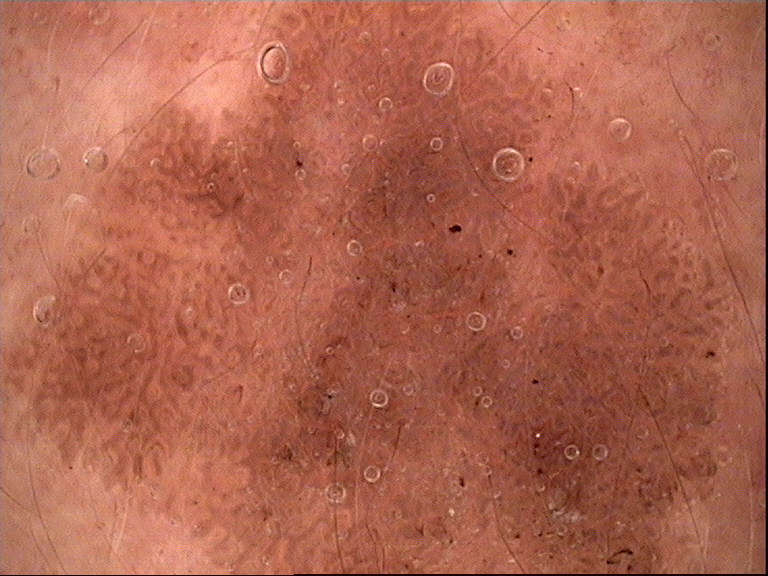Labeled as a seborrheic keratosis.